FST IV, the lesion is associated with itching, the lesion involves the leg, the lesion is described as raised or bumpy, this image was taken at an angle.
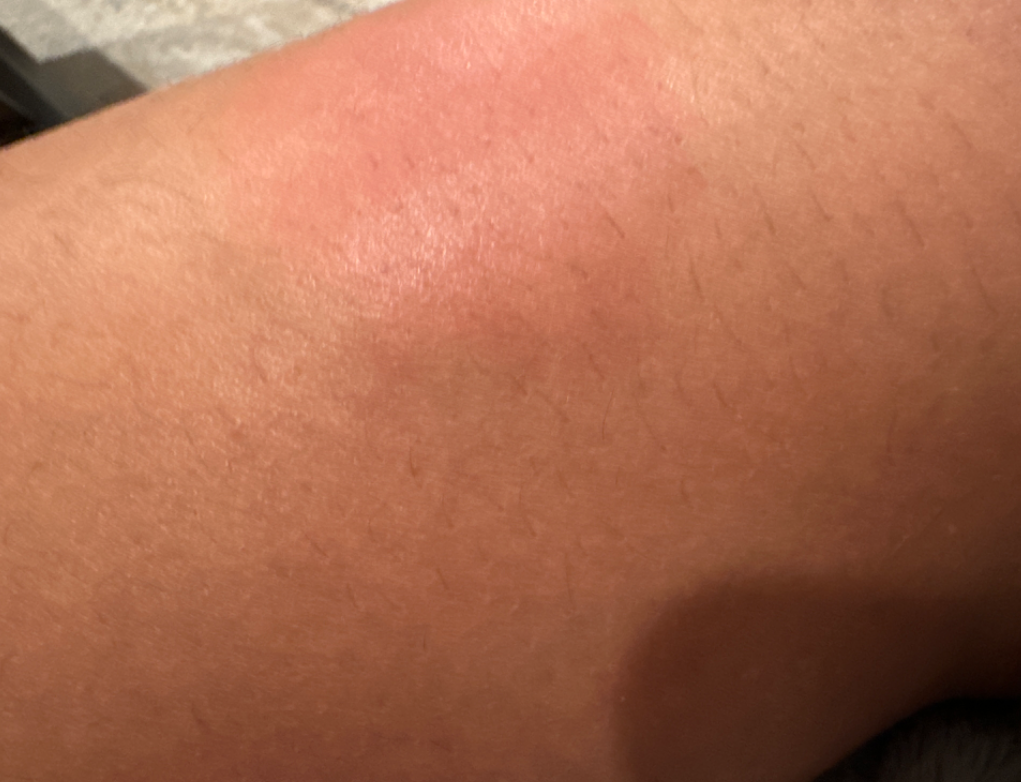  differential:
    tied_lead:
      - Cellulitis
      - Insect Bite
    unlikely:
      - Acute dermatitis, NOS
      - Erythema nodosum
      - Drug Rash